Dermoscopy of a skin lesion.
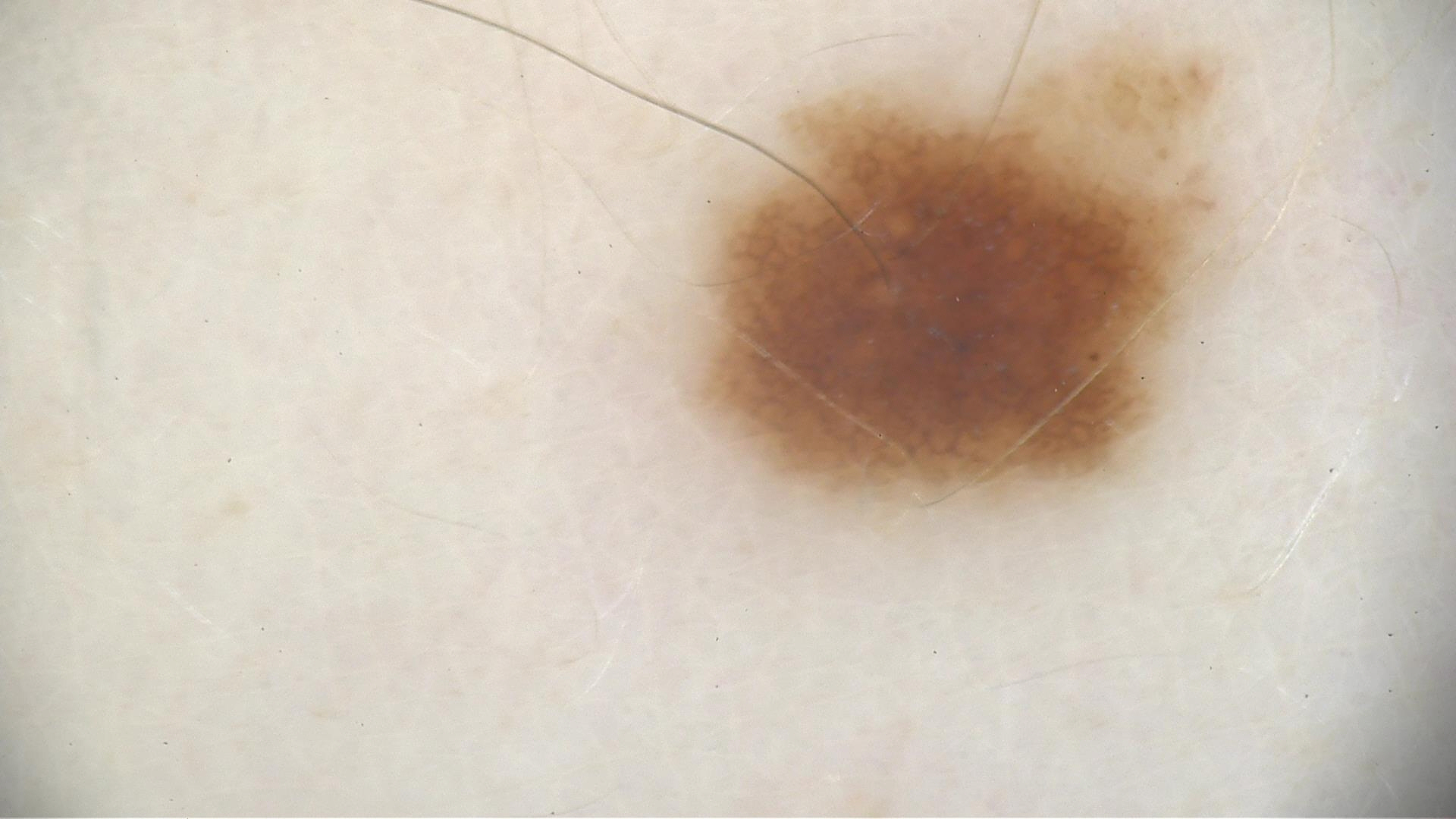This is a banal lesion.
Consistent with a compound nevus.